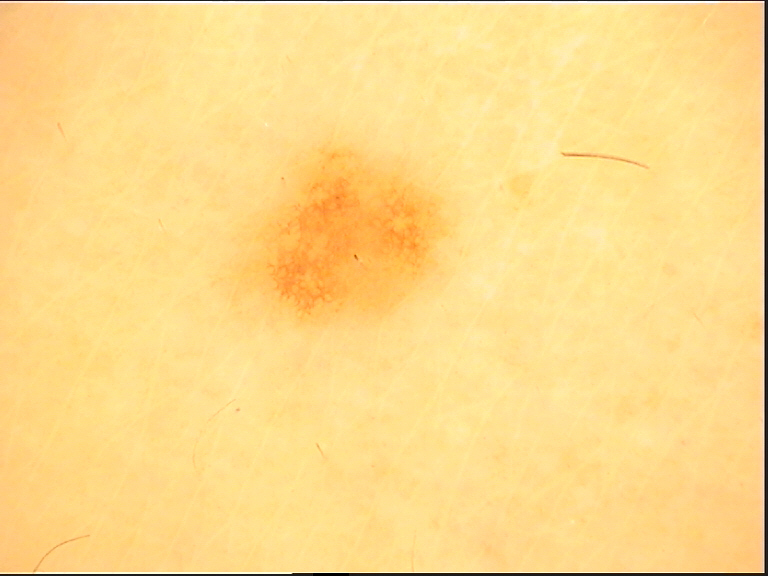Summary:
A dermoscopic photograph of a skin lesion.
Conclusion:
The diagnosis was a dysplastic junctional nevus.